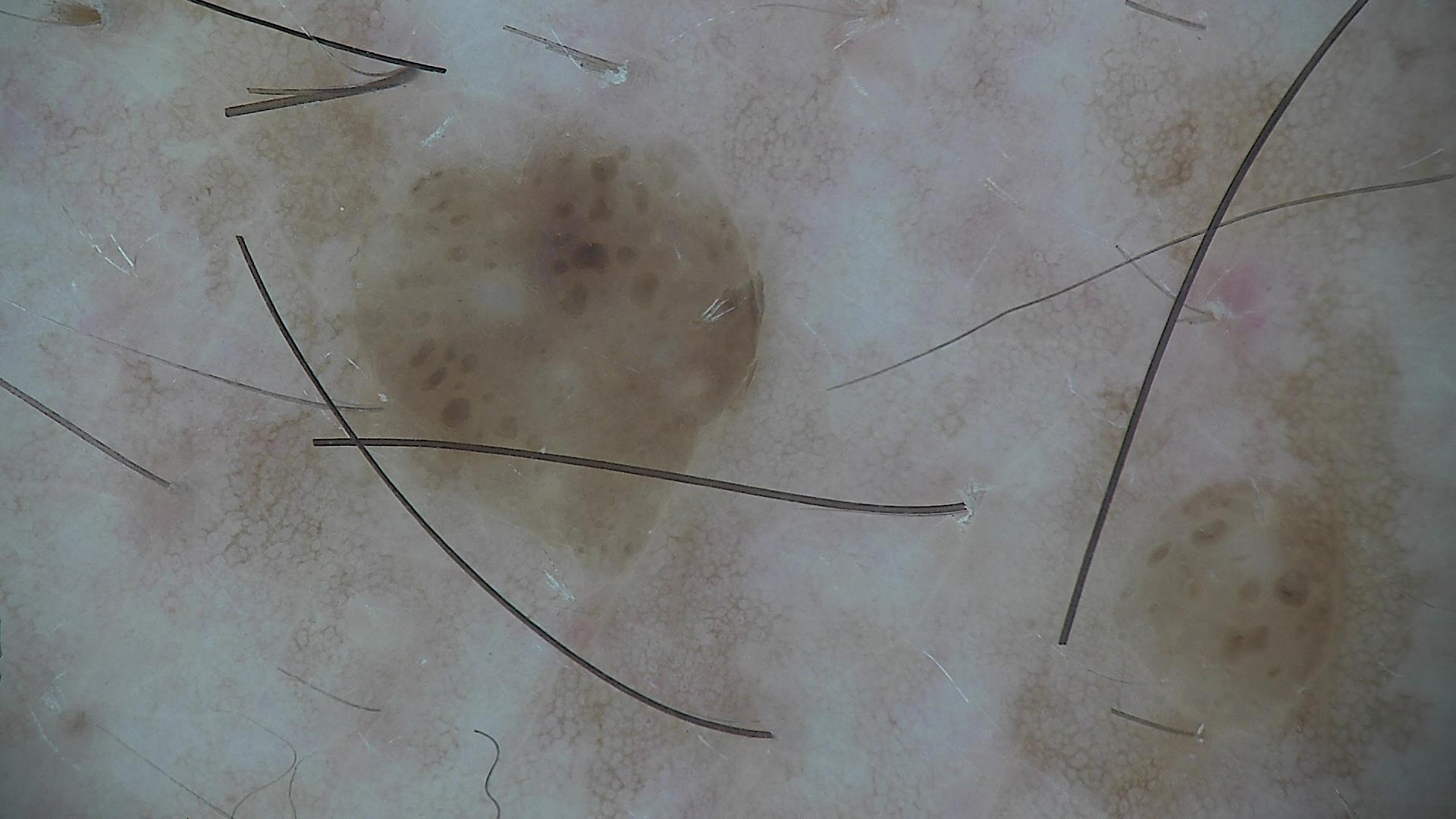  image: dermoscopy
  lesion_type:
    main_class: keratinocytic
  diagnosis:
    name: seborrheic keratosis
    code: sk
    malignancy: benign
    super_class: non-melanocytic
    confirmation: expert consensus